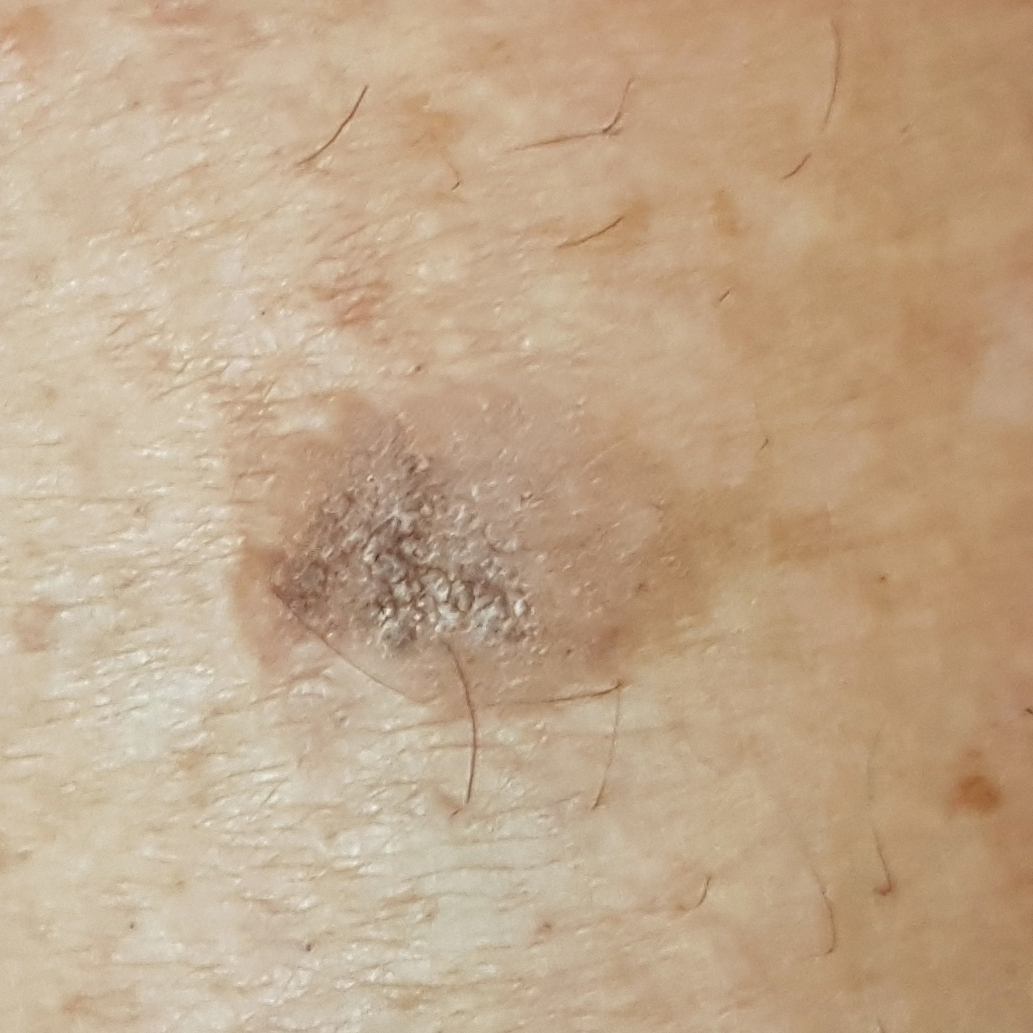Case summary: A clinical close-up photograph of a skin lesion. The lesion is roughly 6 by 6 mm. By the patient's account, the lesion is elevated, but has not bled. Conclusion: The diagnostic impression was a seborrheic keratosis.